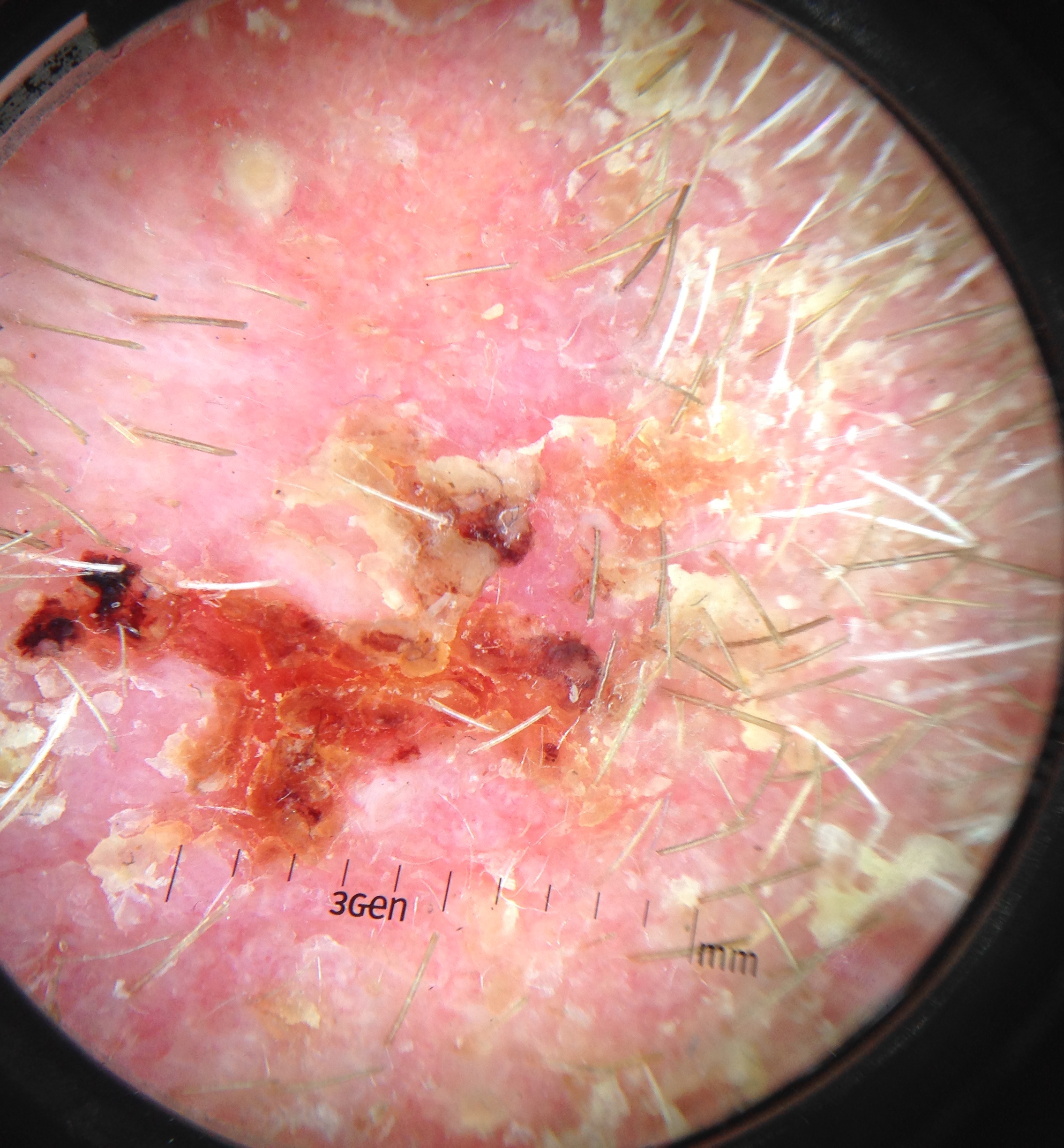Q: What is this lesion?
A: squamous cell carcinoma (biopsy-proven)